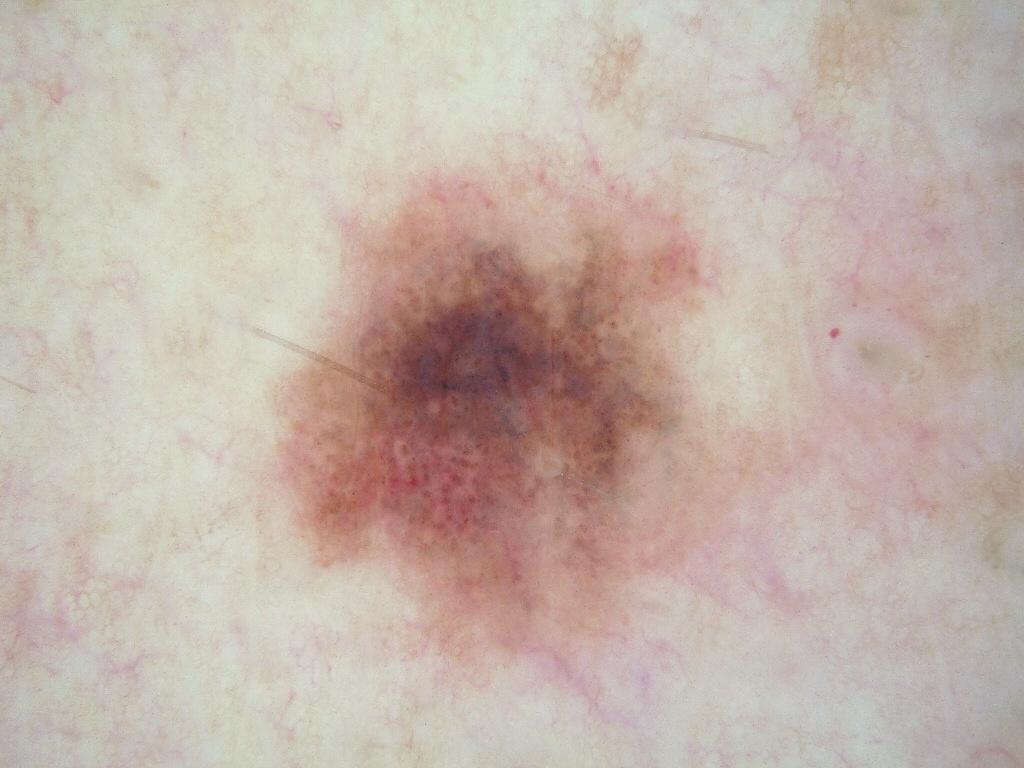A male patient about 30 years old. This is a dermoscopic photograph of a skin lesion. A mid-sized lesion within the field. With coordinates (x1, y1, x2, y2), the lesion's extent is 246, 144, 786, 703. The dermoscopic pattern shows globules, with no pigment network, streaks, negative network, or milia-like cysts. Expert review diagnosed this as a melanocytic nevus.